Few moles overall by the patient's own estimate; collected as part of a research study, without a referral diagnosis; a dermoscopic image of a skin lesion; a female patient aged 48:
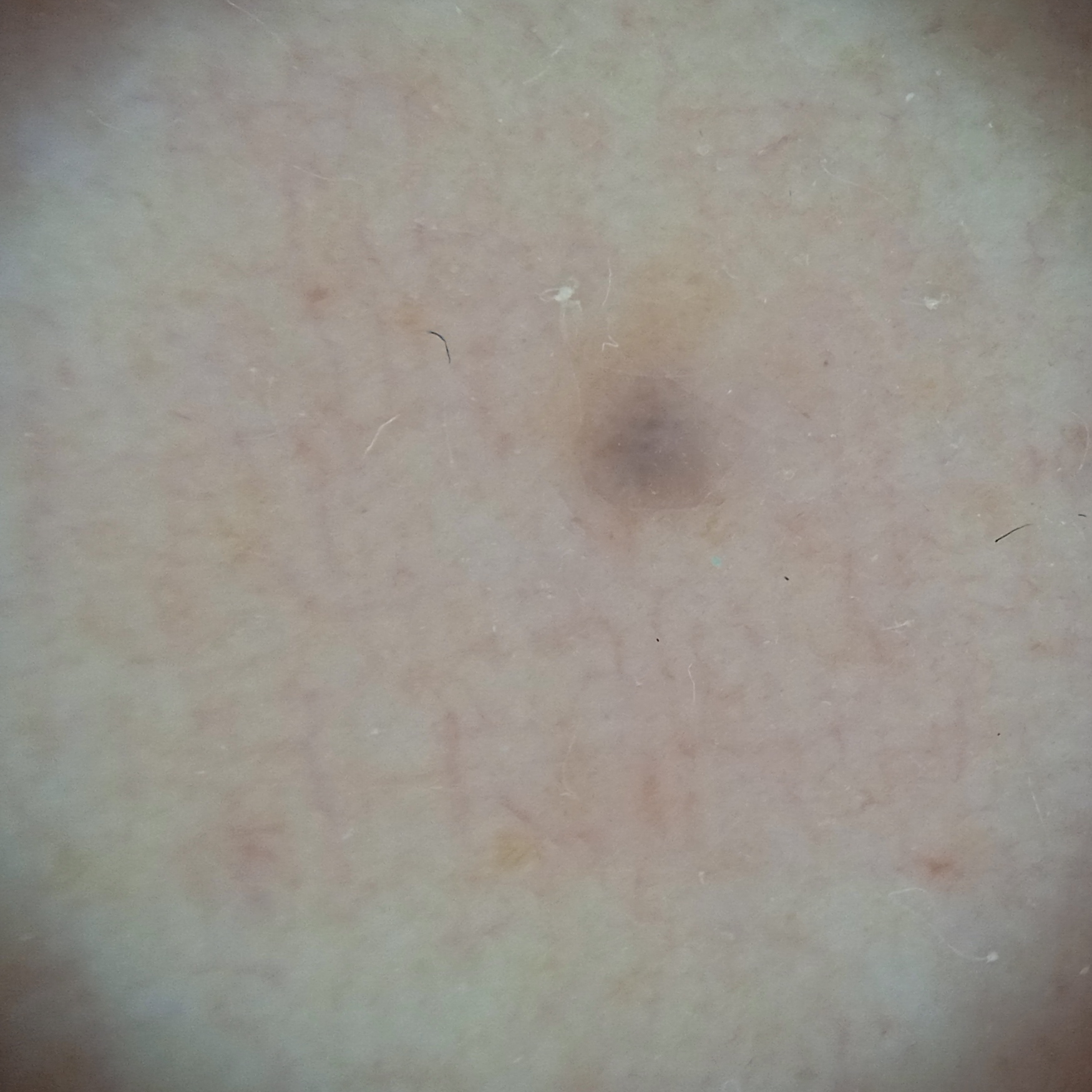{
  "diagnosis": {
    "name": "melanocytic nevus",
    "malignancy": "benign"
  }
}